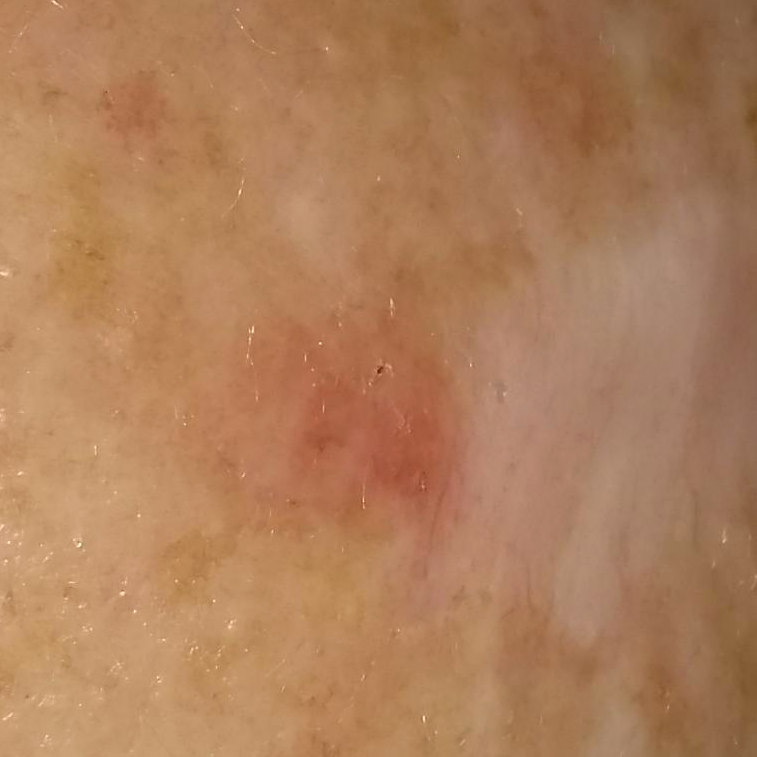skin phototype — II; patient — female, 53 years of age; risk factors — prior malignancy (patient or family), prior skin cancer (patient or family), no pesticide exposure, no alcohol use; image type — smartphone clinical photo; location — the chest; reported symptoms — itching, growth; diagnosis — basal cell carcinoma (biopsy-proven).